Male subject, age 18–29. This is a close-up image. The lesion involves the back of the hand:
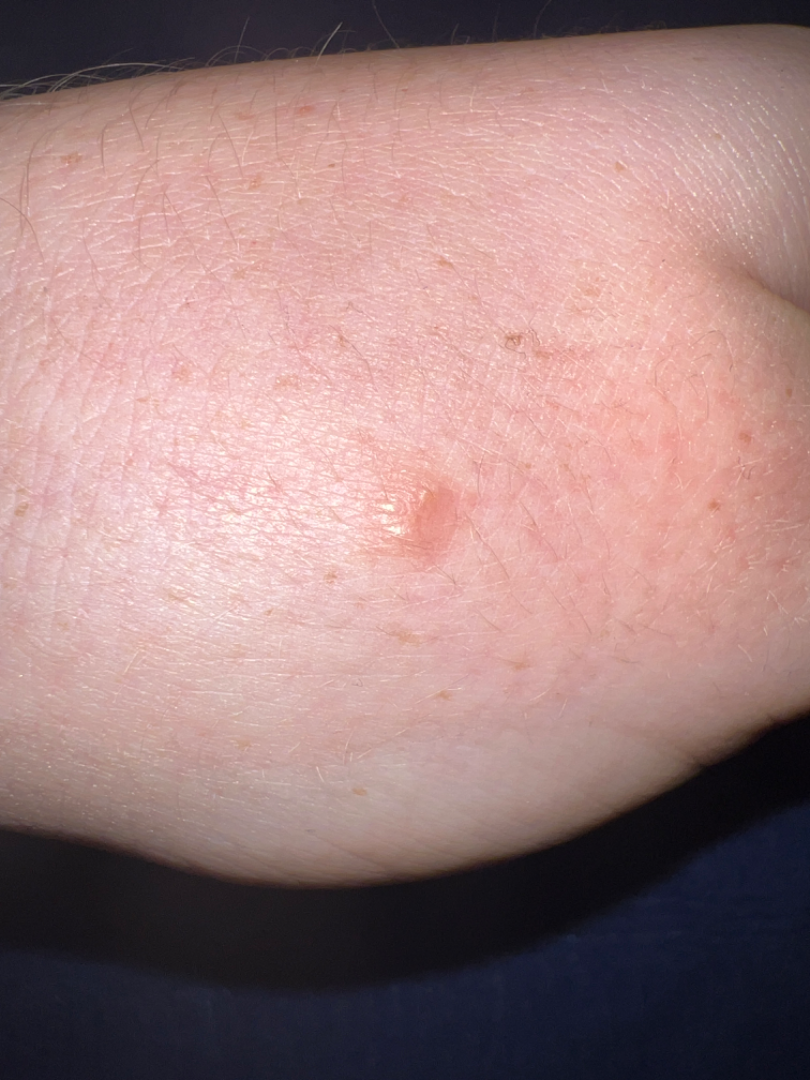<summary>
<symptoms>itching</symptoms>
<texture>raised or bumpy</texture>
<duration>one to four weeks</duration>
<differential>
  <tied_lead>Insect Bite, Melanocytic Nevus, Basal Cell Carcinoma</tied_lead>
</differential>
</summary>